A clinical photograph of a skin lesion; Fitzpatrick II; a male subject about 85 years old or older: 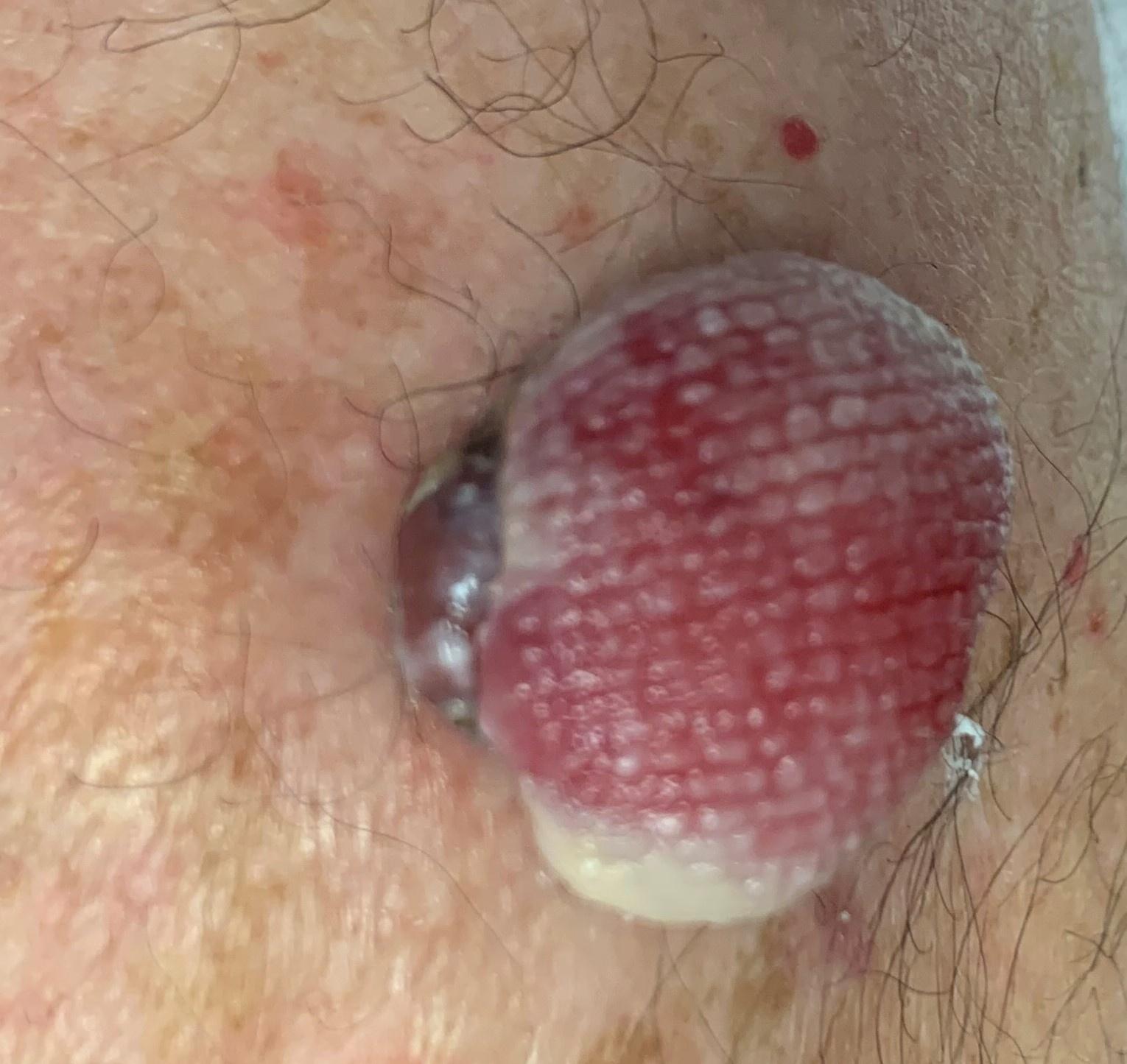Clinical context:
Located on an upper extremity.
Conclusion:
Biopsy-confirmed as a melanoma.